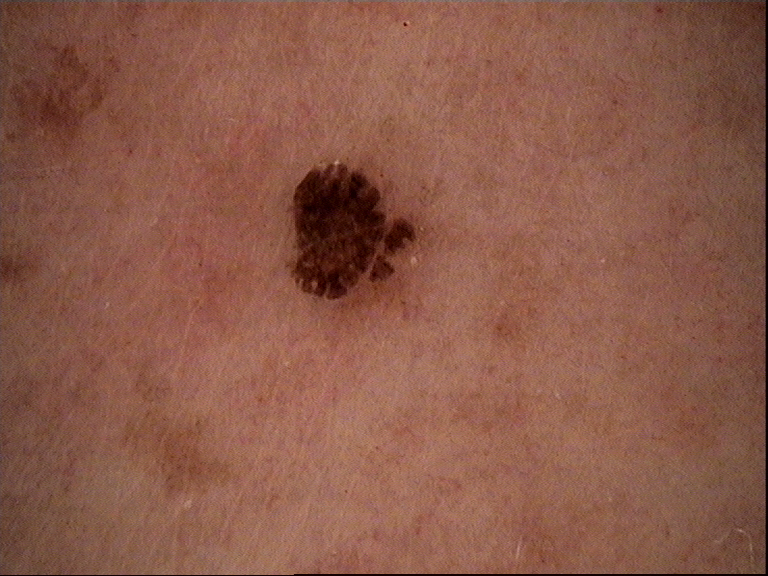Q: What is the imaging modality?
A: dermatoscopy
Q: What was the diagnostic impression?
A: seborrheic keratosis (expert consensus)